A subject 74 years old — 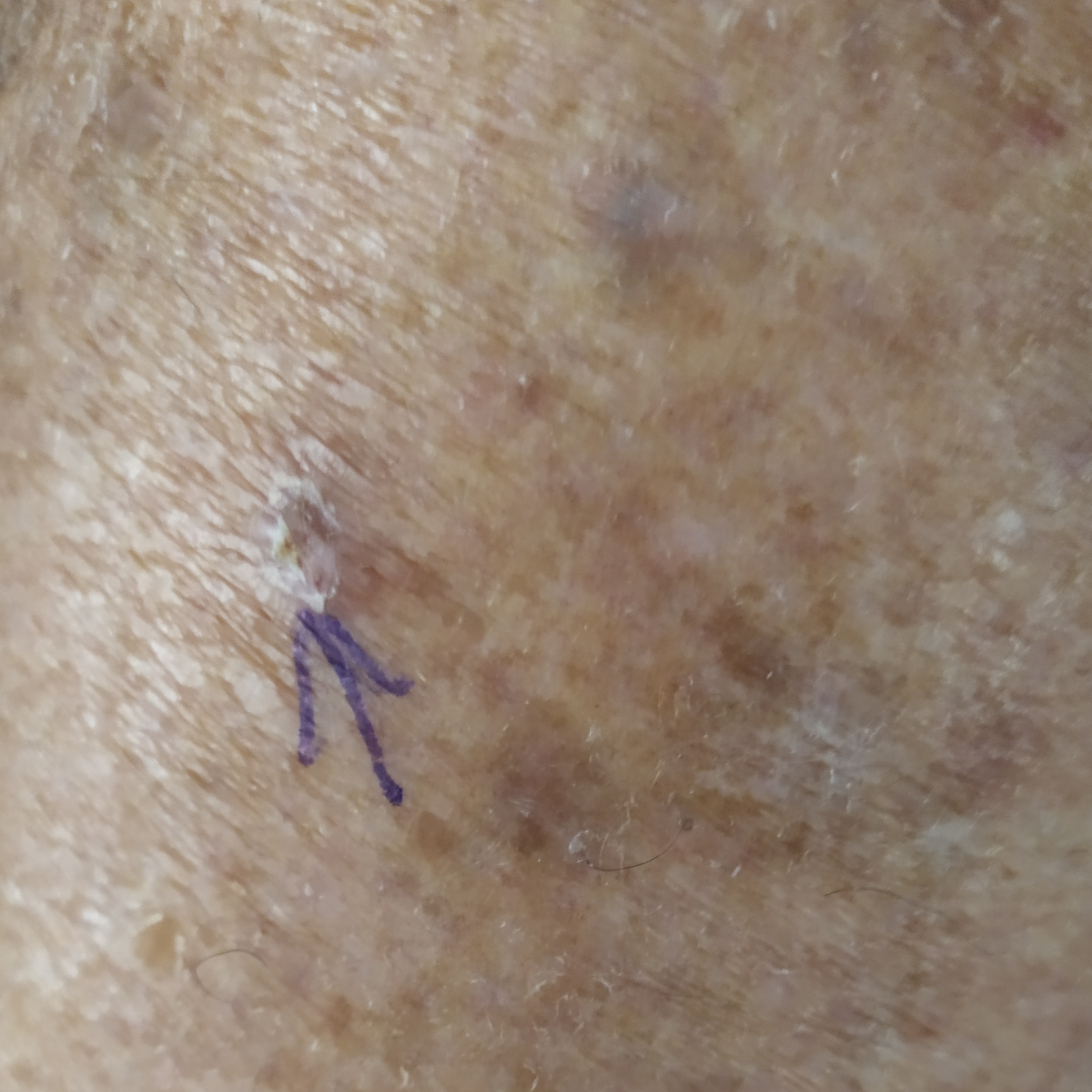{"lesion_location": "a thigh", "symptoms": {"present": ["itching"]}, "diagnosis": {"name": "actinic keratosis", "code": "ACK", "malignancy": "indeterminate", "confirmation": "clinical consensus"}}